Dermoscopy of a skin lesion: 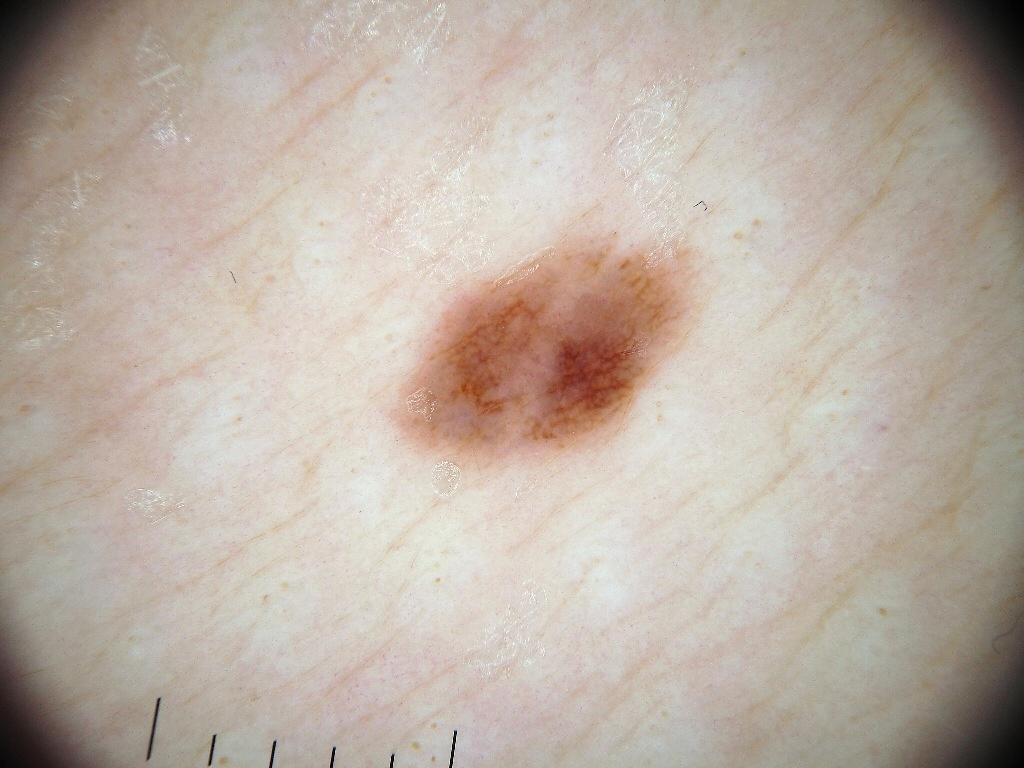Case summary:
The dermoscopic pattern shows pigment network; no globules, streaks, negative network, or milia-like cysts. In (x1, y1, x2, y2) order, the visible lesion spans <box>389, 231, 703, 471</box>. A small lesion within a wider field of skin.
Conclusion:
Clinically diagnosed as a melanocytic nevus, a benign skin lesion.